The photograph is a close-up of the affected area: 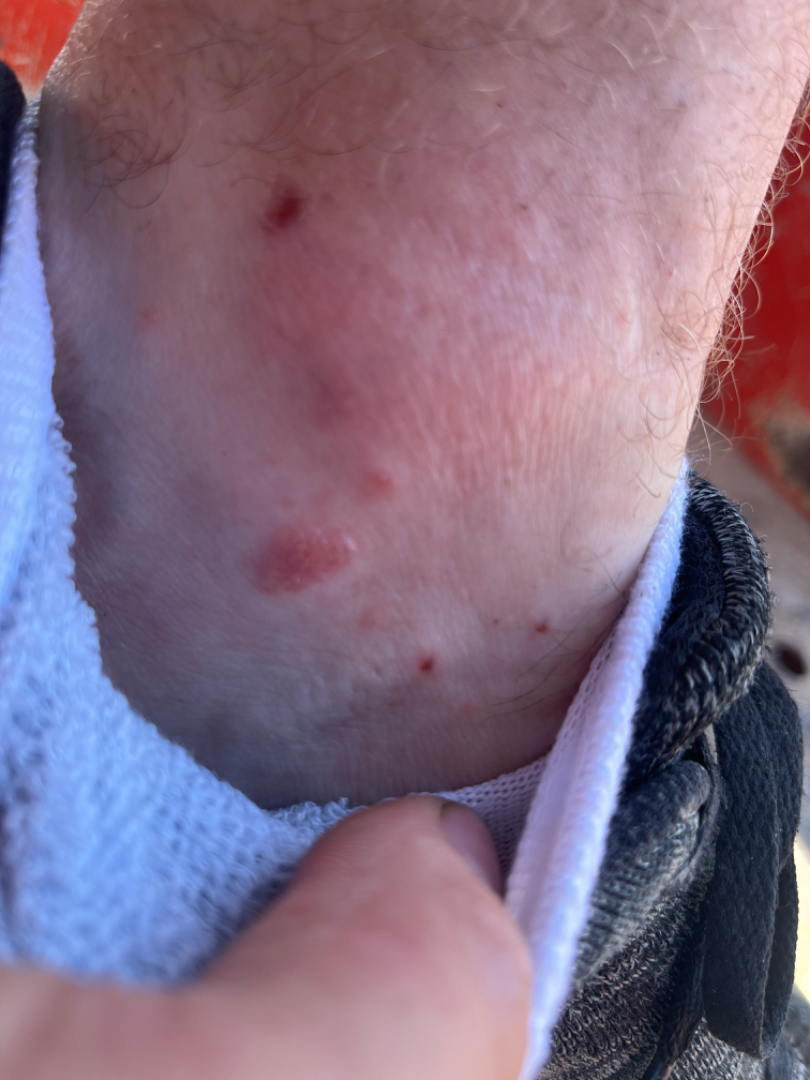The reviewing dermatologist was unable to assign a differential diagnosis from the image.